Dermoscopy of a skin lesion.
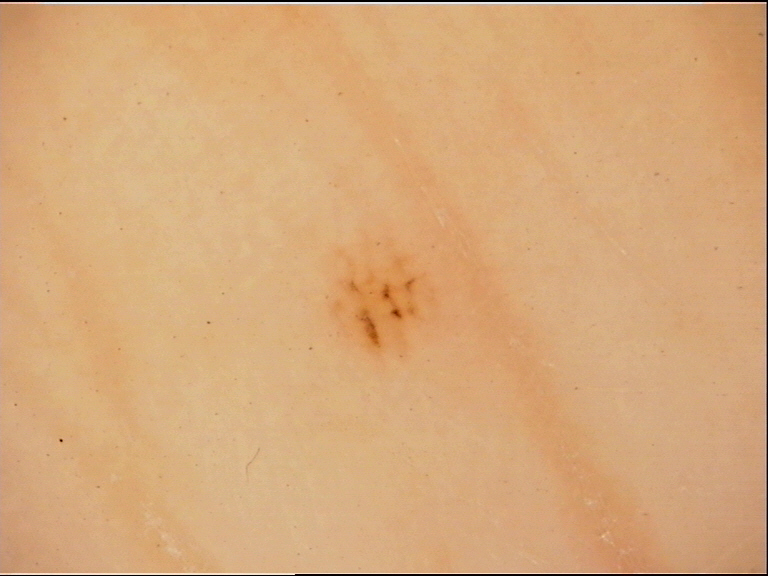<lesion>
  <lesion_type>
    <main_class>banal</main_class>
    <pattern>junctional</pattern>
  </lesion_type>
  <diagnosis>
    <name>acral junctional nevus</name>
    <code>ajb</code>
    <malignancy>benign</malignancy>
    <super_class>melanocytic</super_class>
    <confirmation>expert consensus</confirmation>
  </diagnosis>
</lesion>